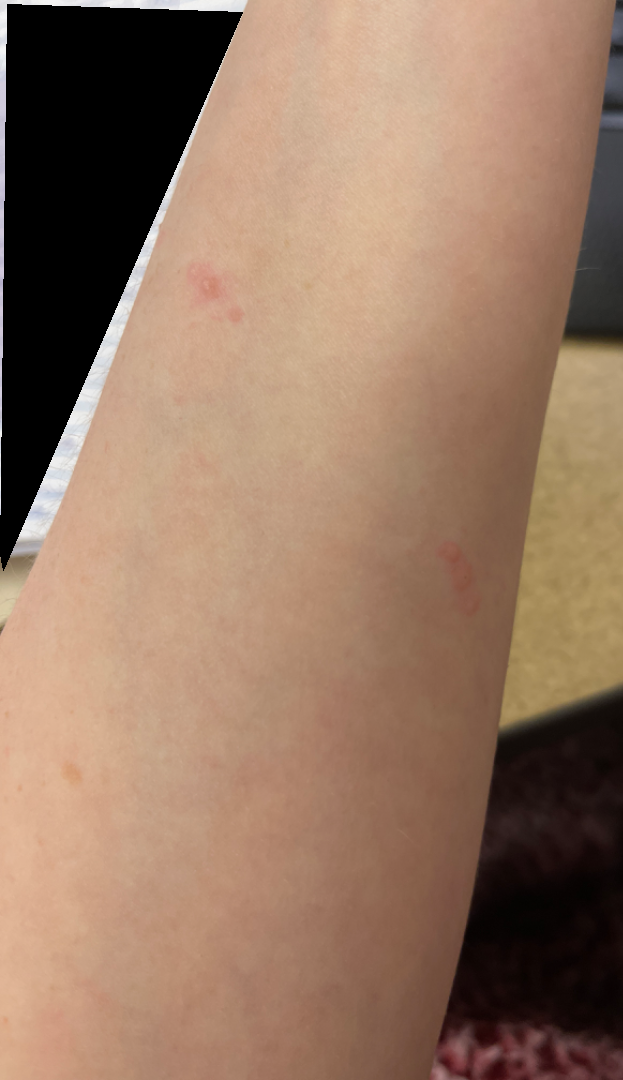Notes:
- assessment — indeterminate from the photograph
- view — close-up